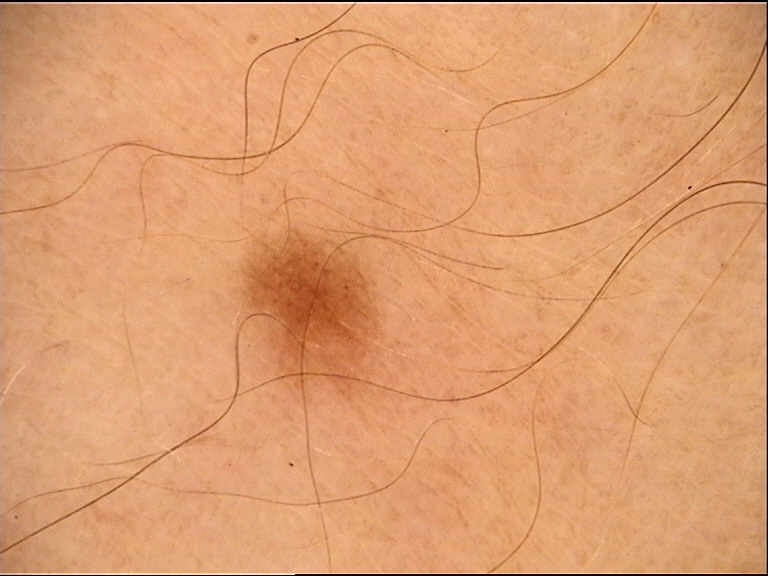A dermoscopy image of a single skin lesion. The morphology is that of a banal lesion. The diagnostic label was a junctional nevus.